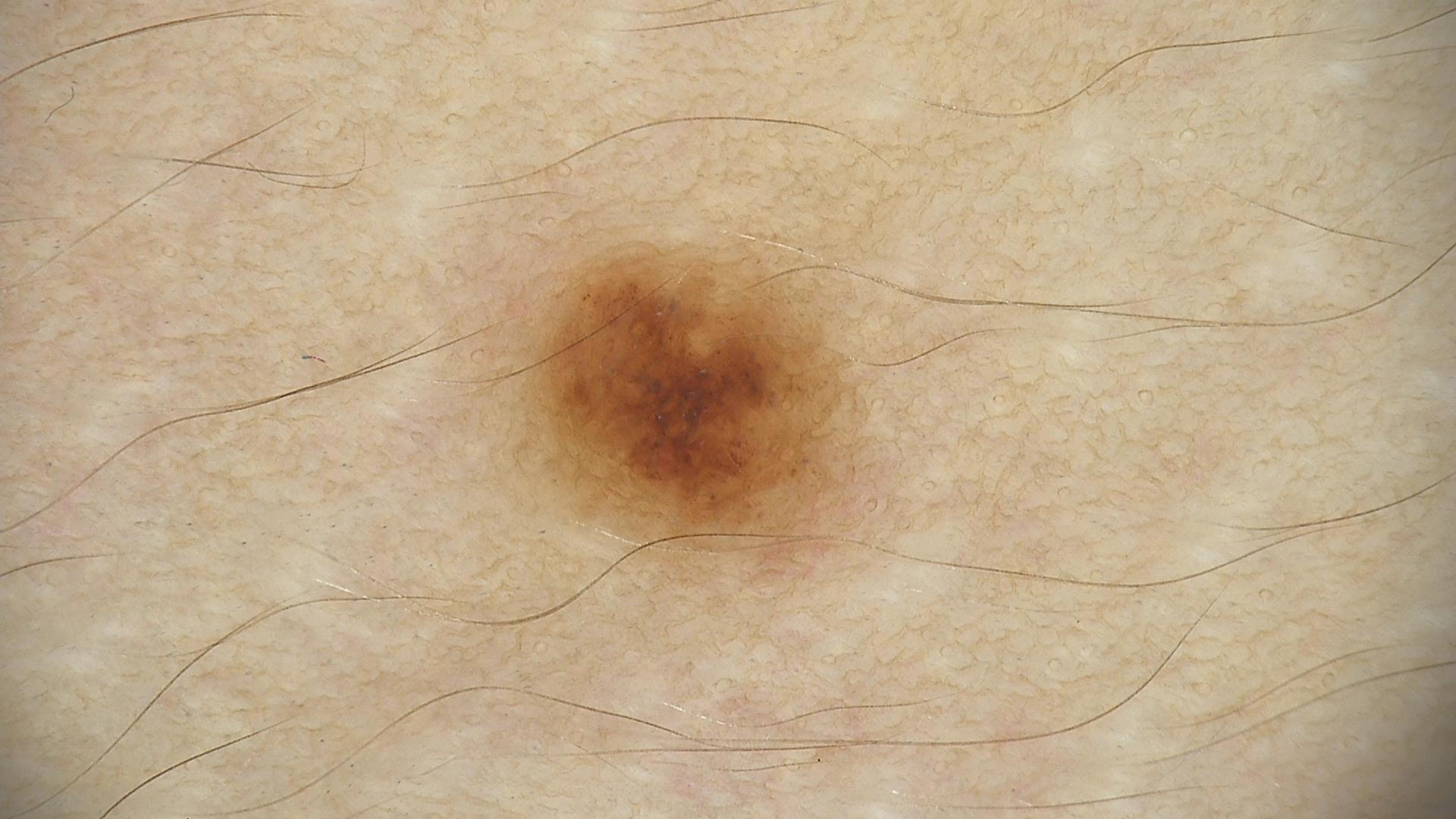Labeled as a compound nevus.